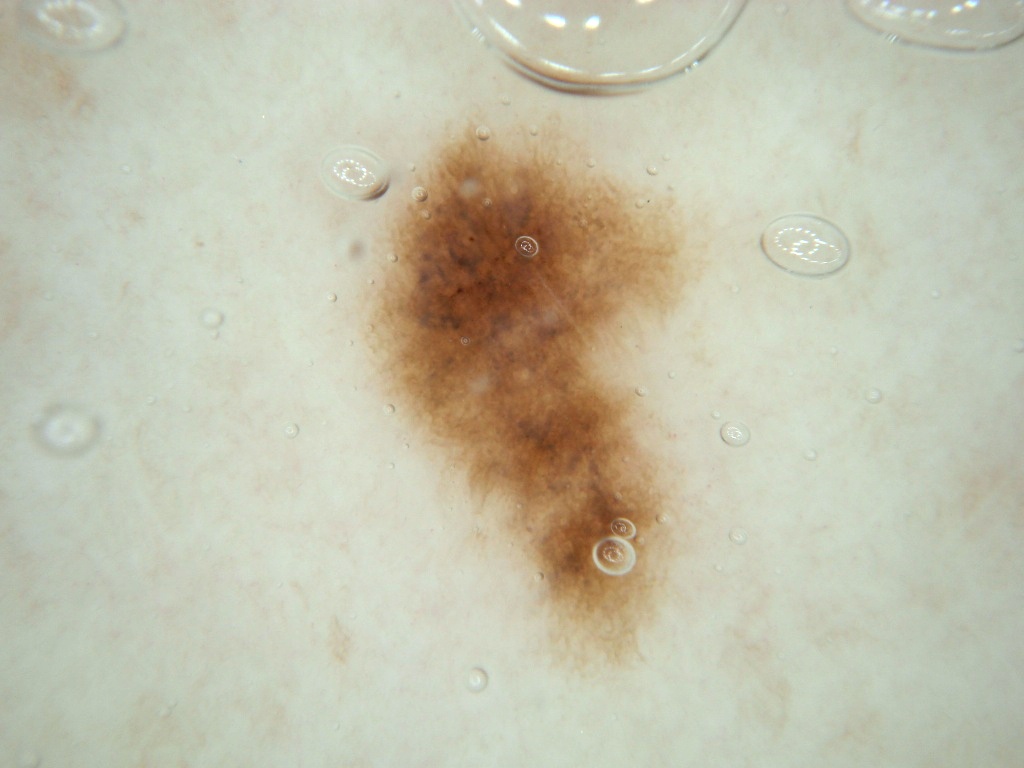Dermoscopy of a skin lesion.
The lesion's extent is left=361, top=112, right=690, bottom=664.
Diagnosed as a benign lesion.